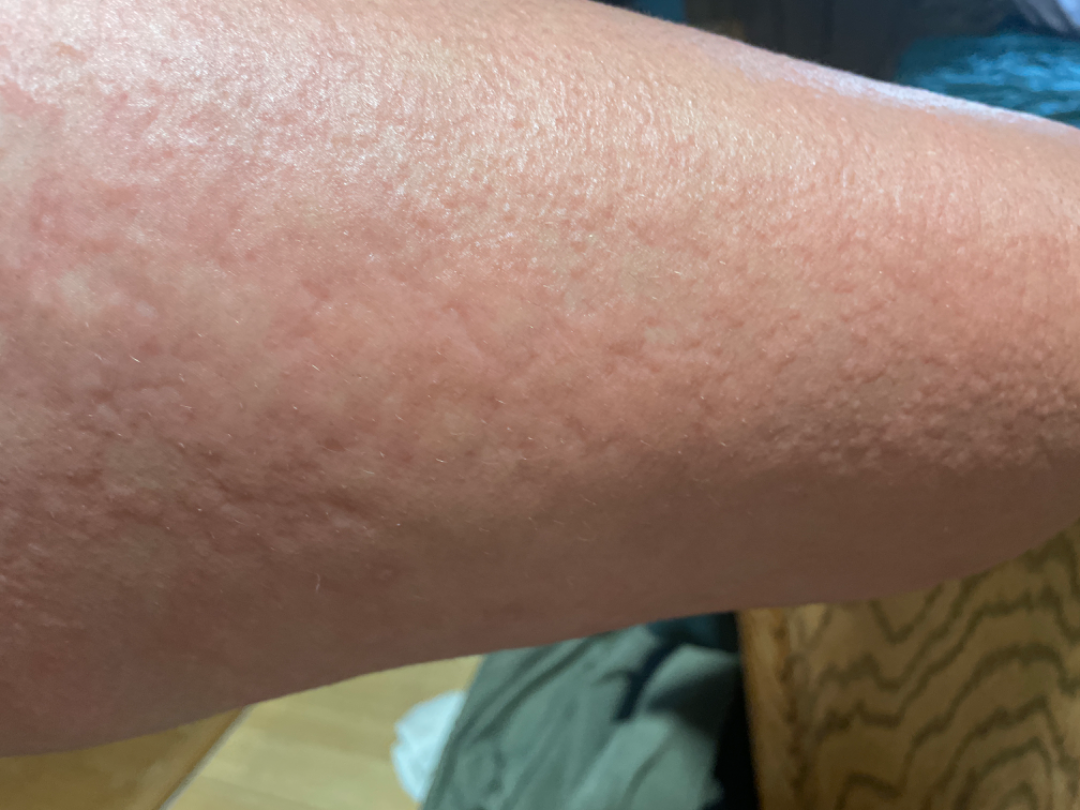History: The patient reported no systemic symptoms. Close-up view. The patient considered this a rash. The lesion is described as raised or bumpy. Located on the arm and leg. Impression: On teledermatology review: Urticaria (55%); Allergic Contact Dermatitis (27%); Bullous Pemphigoid (18%).